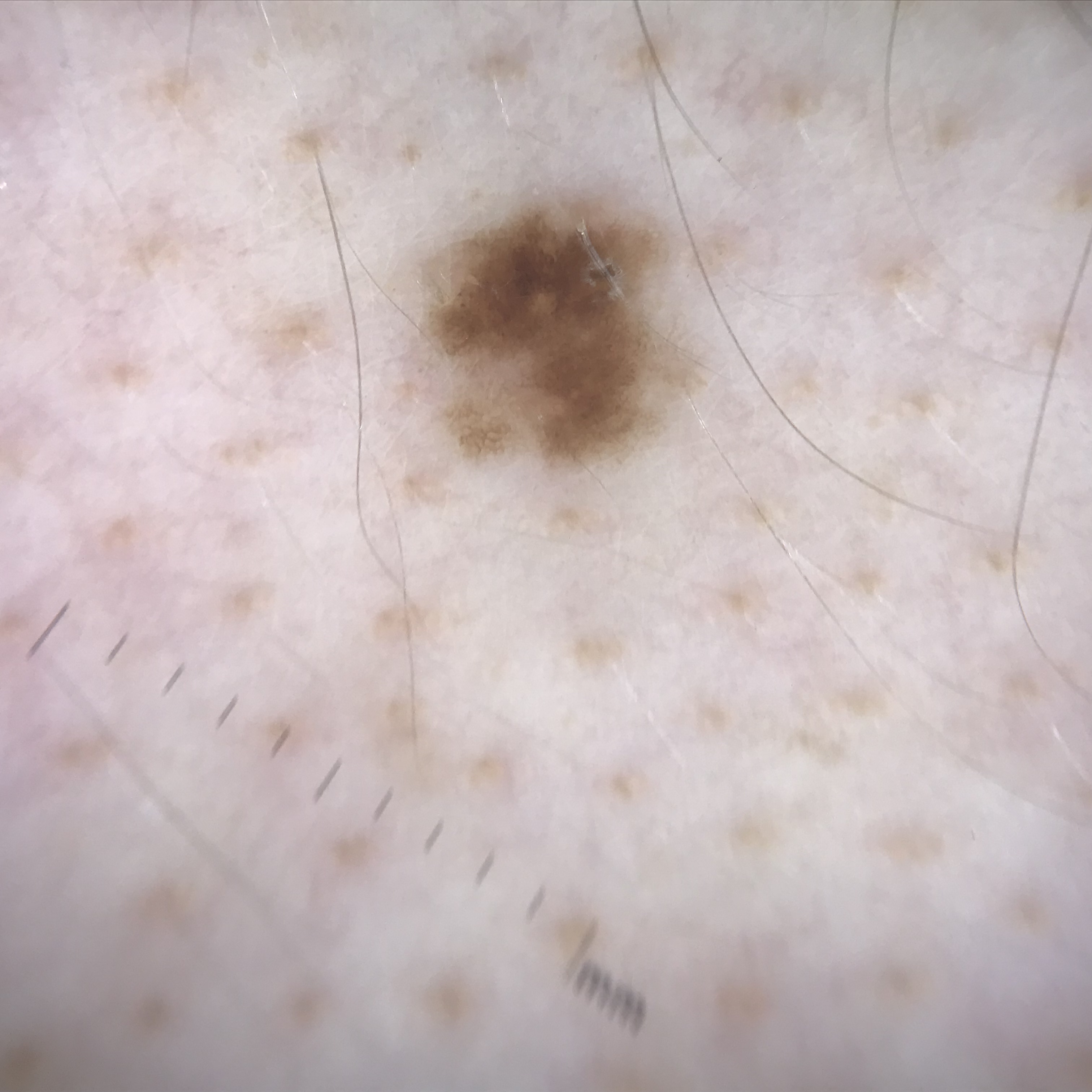modality = dermoscopy
assessment = dysplastic junctional nevus (expert consensus)